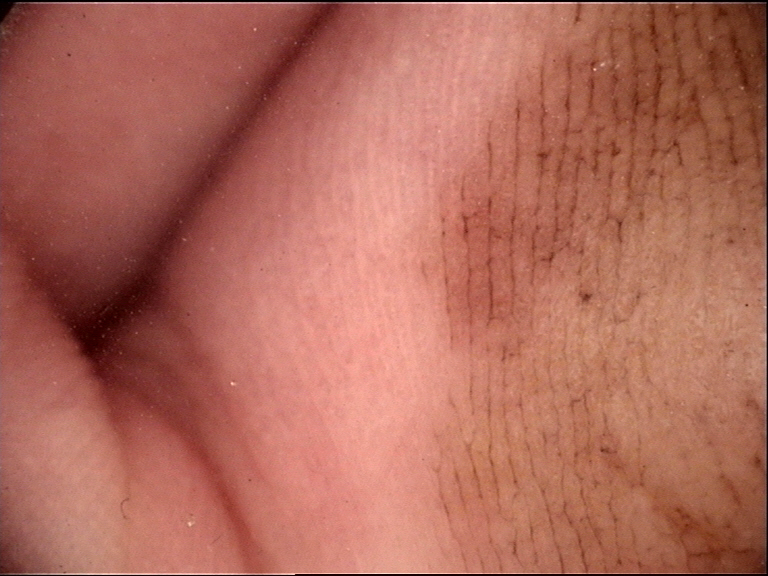{
  "diagnosis": {
    "name": "acral junctional nevus",
    "code": "ajb",
    "malignancy": "benign",
    "super_class": "melanocytic",
    "confirmation": "expert consensus"
  }
}